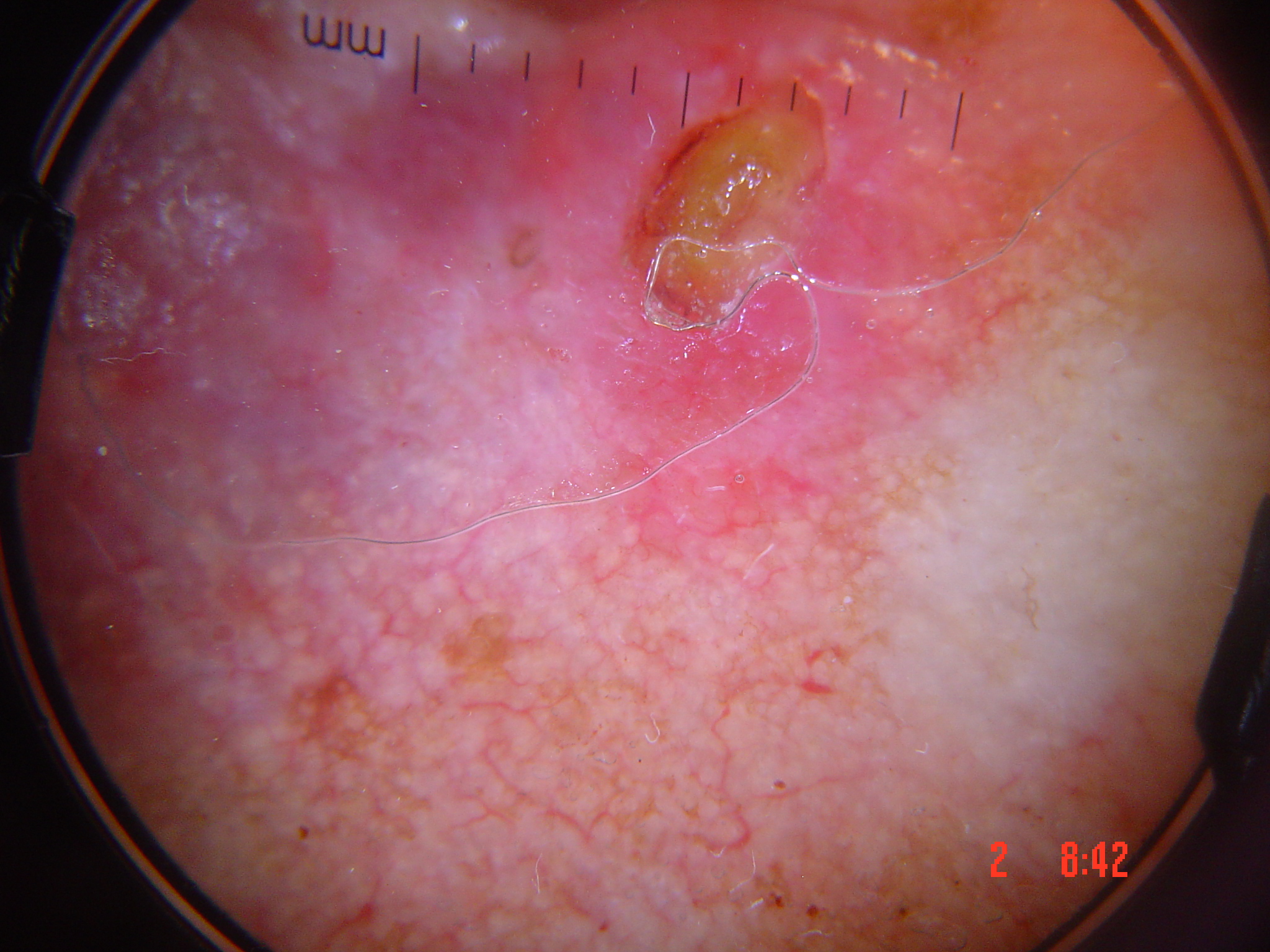diagnosis=squamous cell carcinoma (biopsy-proven)